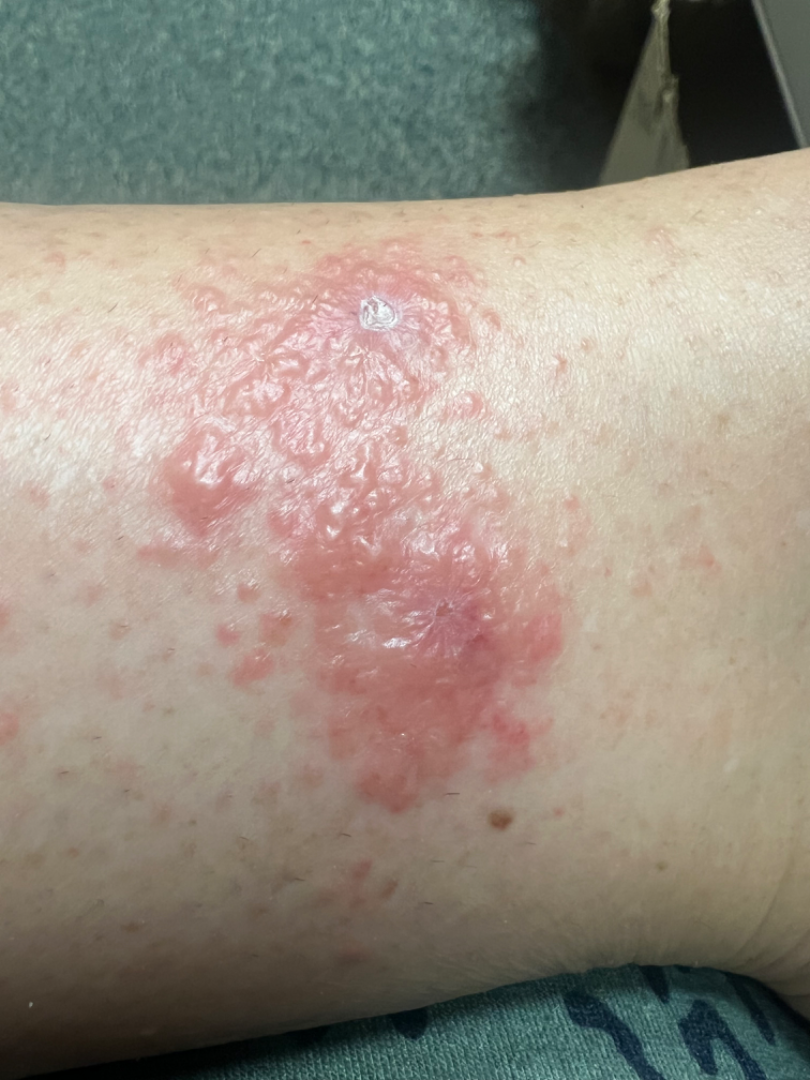<report>
  <duration>one to four weeks</duration>
  <texture>fluid-filled</texture>
  <body_site>leg</body_site>
  <shot_type>close-up</shot_type>
  <skin_tone>
    <fitzpatrick>II</fitzpatrick>
    <monk_skin_tone>2, 3</monk_skin_tone>
  </skin_tone>
  <differential>
    <leading>Allergic Contact Dermatitis</leading>
    <considered>Eczema</considered>
  </differential>
</report>